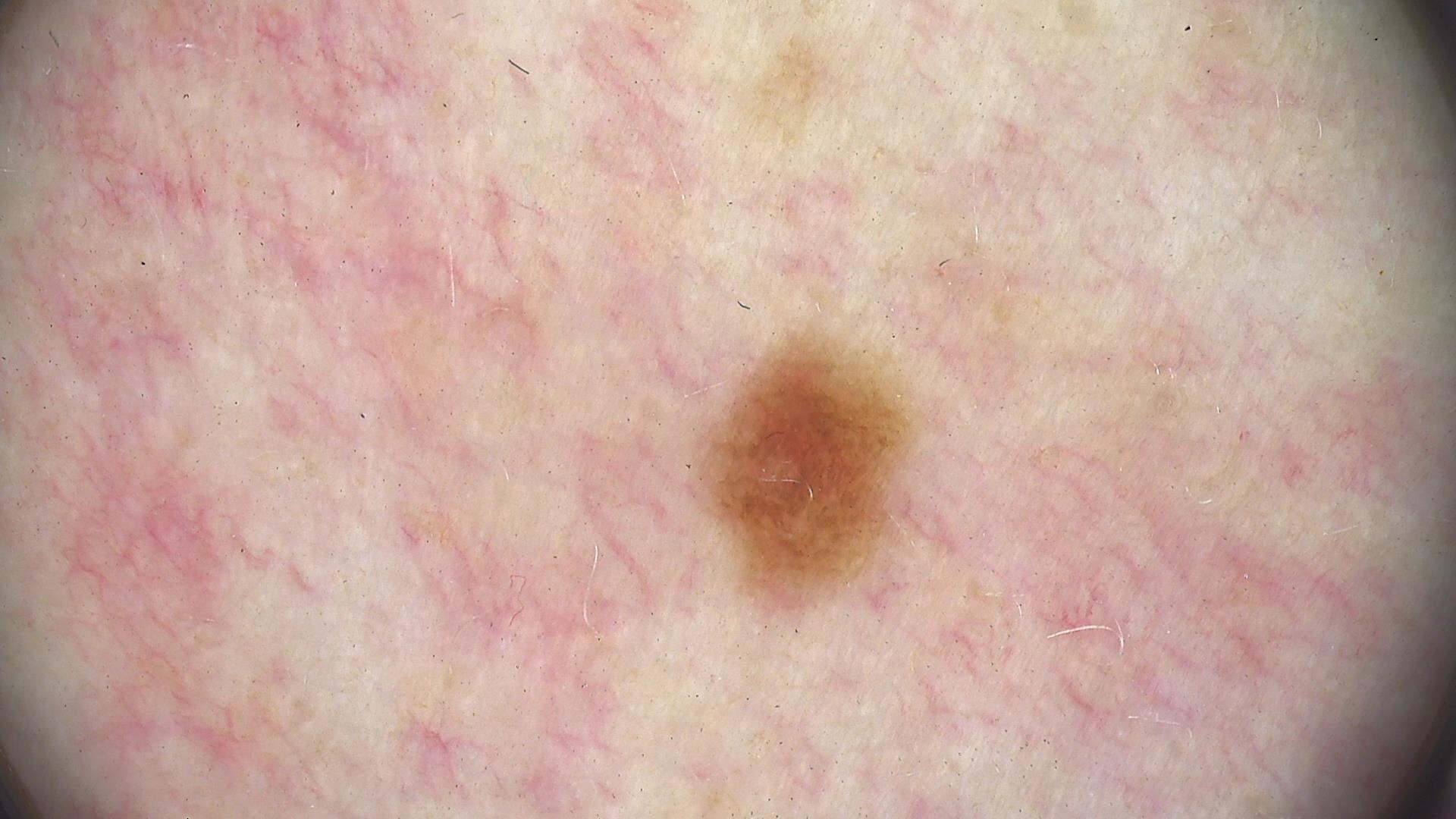Summary:
A skin lesion imaged with a dermatoscope.
Conclusion:
Consistent with a dysplastic junctional nevus.